The lesion involves the back of the torso · an image taken at a distance · female patient, age 18–29 — 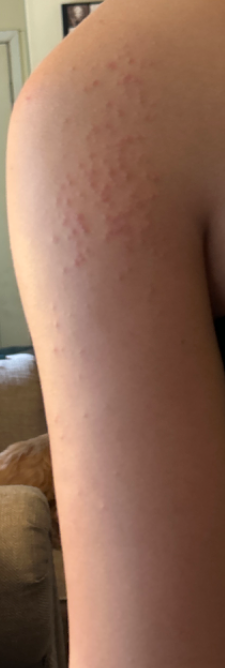Impression: Diagnostic features were not clearly distinguishable in this photograph. History: The patient notes the condition has been present for about one day. No associated systemic symptoms reported. The patient notes burning. The patient described the issue as a rash. The patient notes the lesion is raised or bumpy.